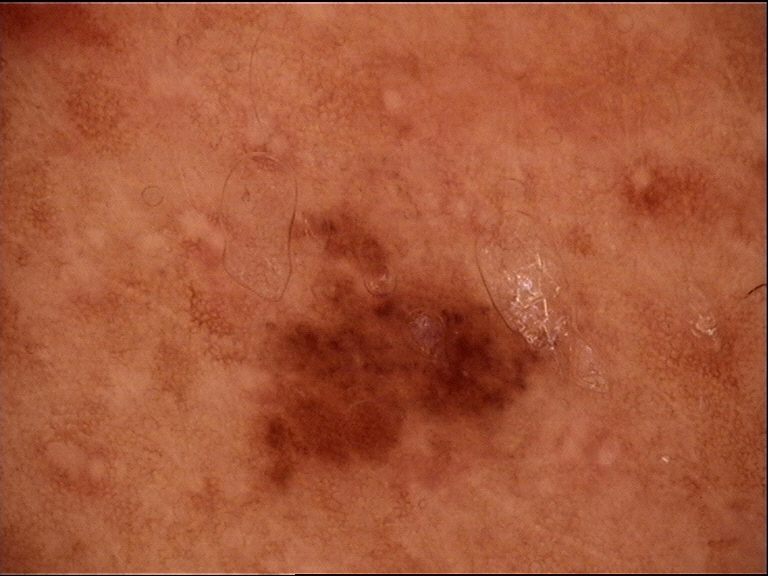Dermoscopy of a skin lesion. Classified as a dysplastic junctional nevus.